The lesion involves the arm, the photograph was taken at an angle.
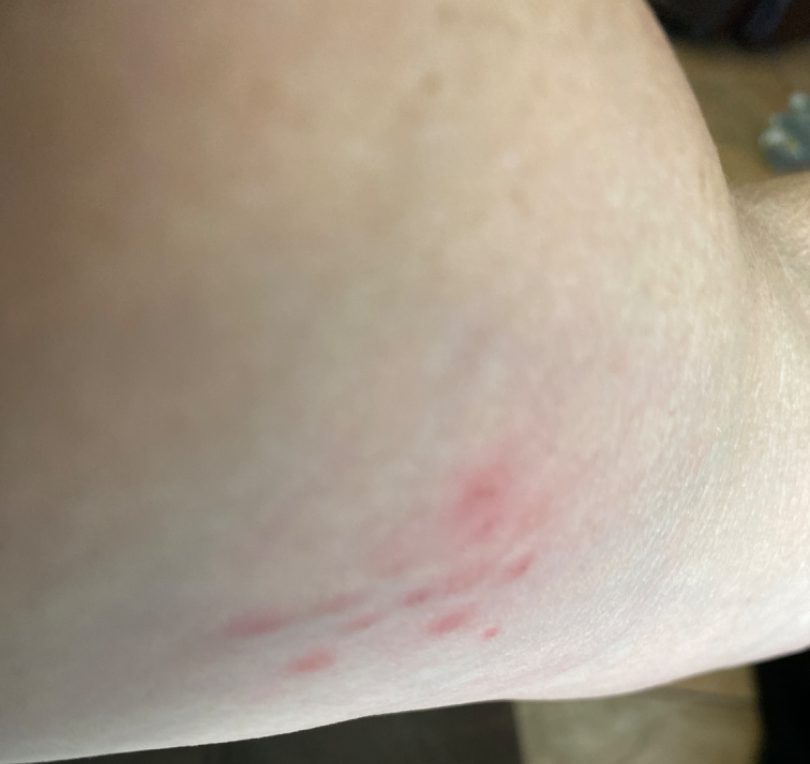On remote review of the image, most likely Insect Bite; the differential also includes Herpes Simplex; less likely is Allergic Contact Dermatitis.